A female subject aged around 35; a dermoscopy image of a single skin lesion.
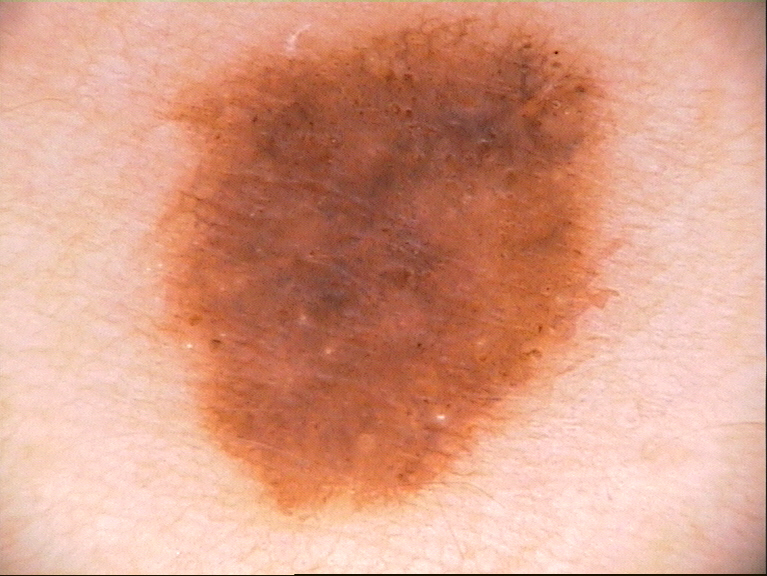Q: How does the lesion relate to the field edge?
A: clipped at the frame edge
Q: Which dermoscopic features were noted?
A: globules and pigment network
Q: Where is the lesion in the image?
A: 154/0/616/513
Q: What is this lesion?
A: a melanocytic nevus